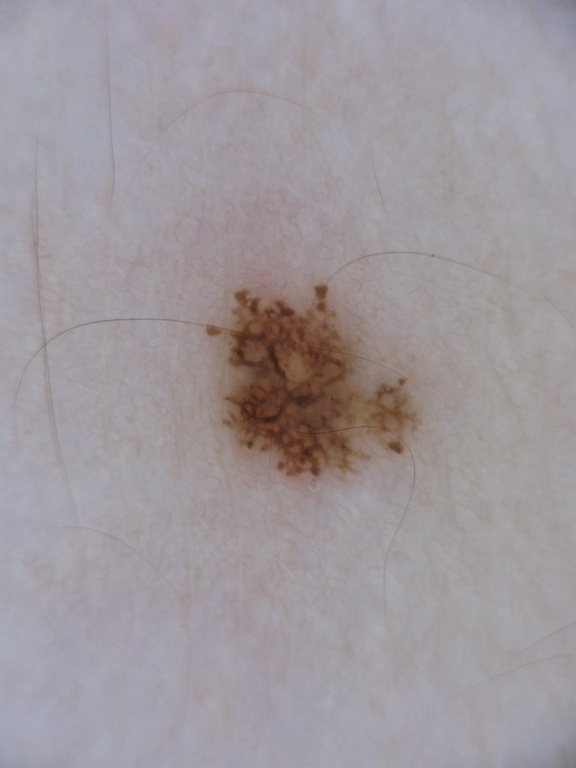Dermoscopy of a skin lesion. As (left, top, right, bottom), lesion location: 203, 281, 417, 480. The dermoscopic pattern shows globules and pigment network. Clinically diagnosed as a melanocytic nevus.